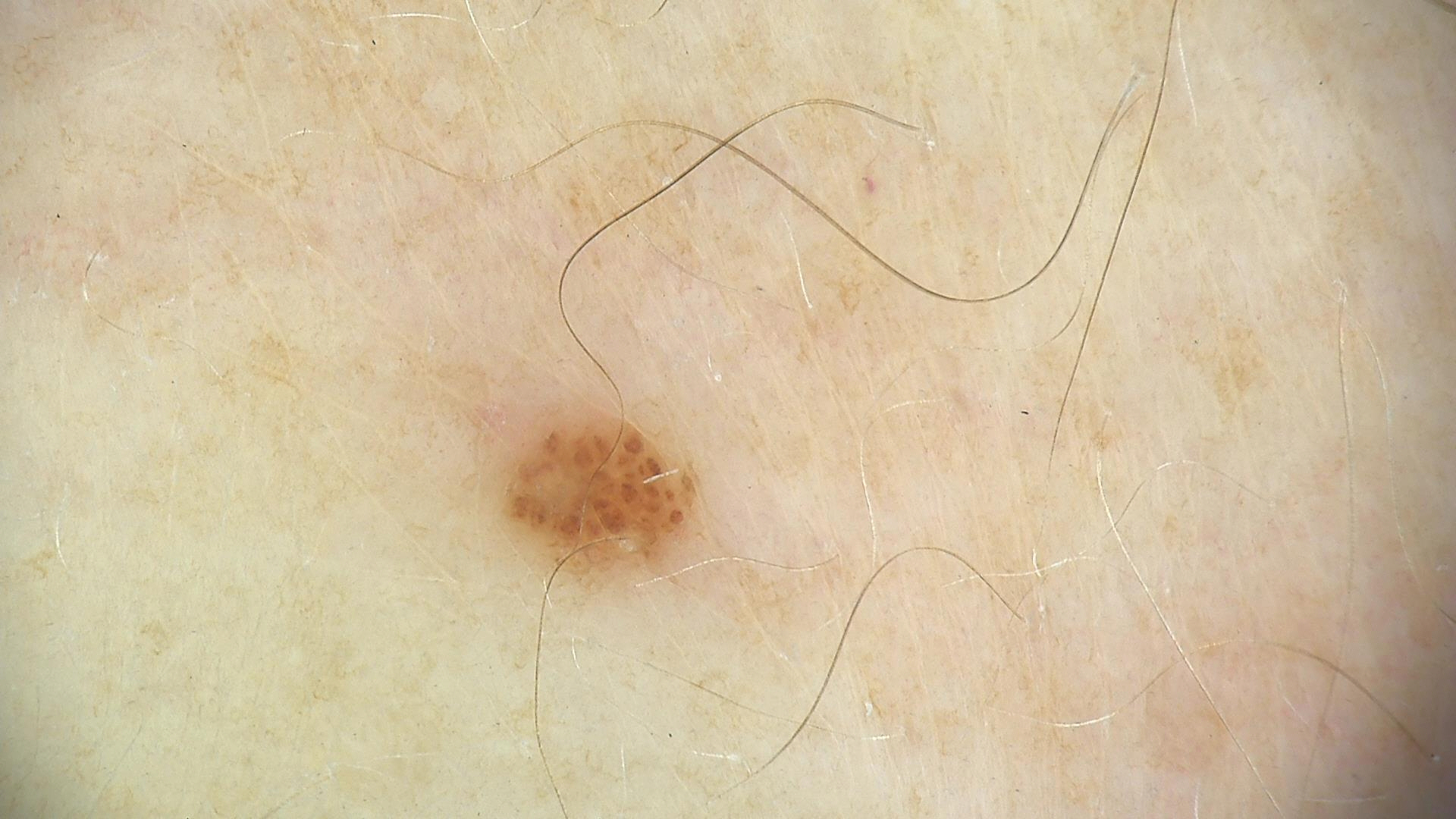The morphology is that of a banal lesion.
Labeled as a junctional nevus.